Close-up view; the affected area is the palm: 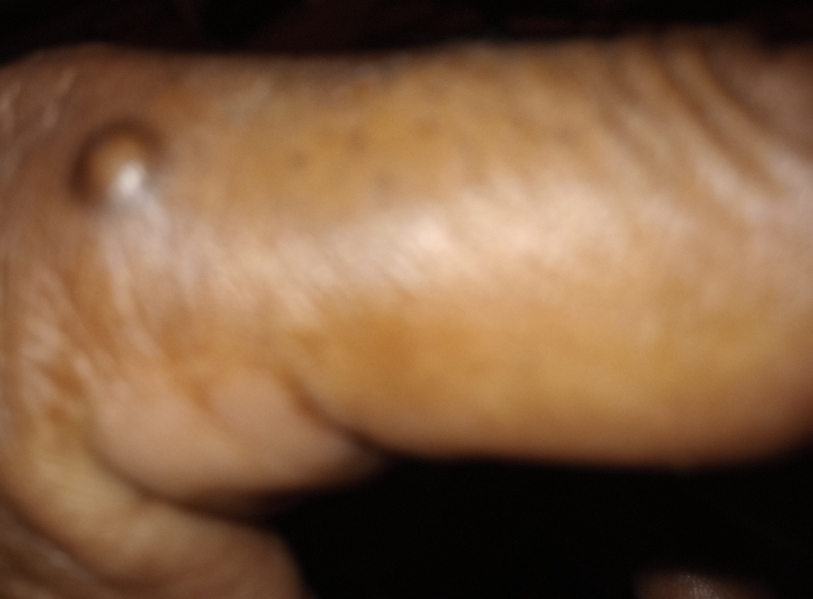assessment: Cyst (55%); Dermatofibroma (27%); Calcinosis cutis (18%).